A female patient 26 years old: 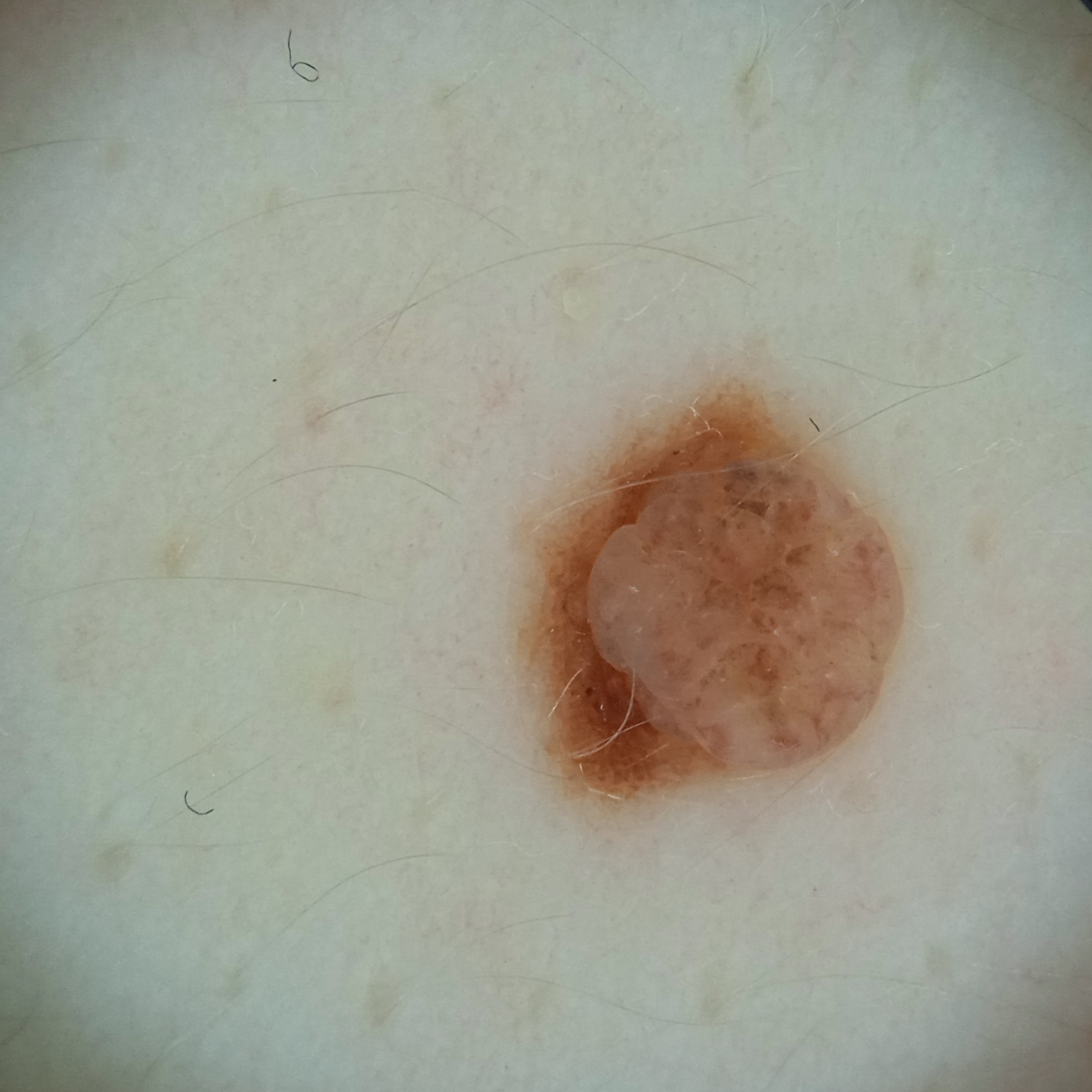The lesion is about 4.5 mm across. The consensus diagnosis for this lesion was a melanocytic nevus.